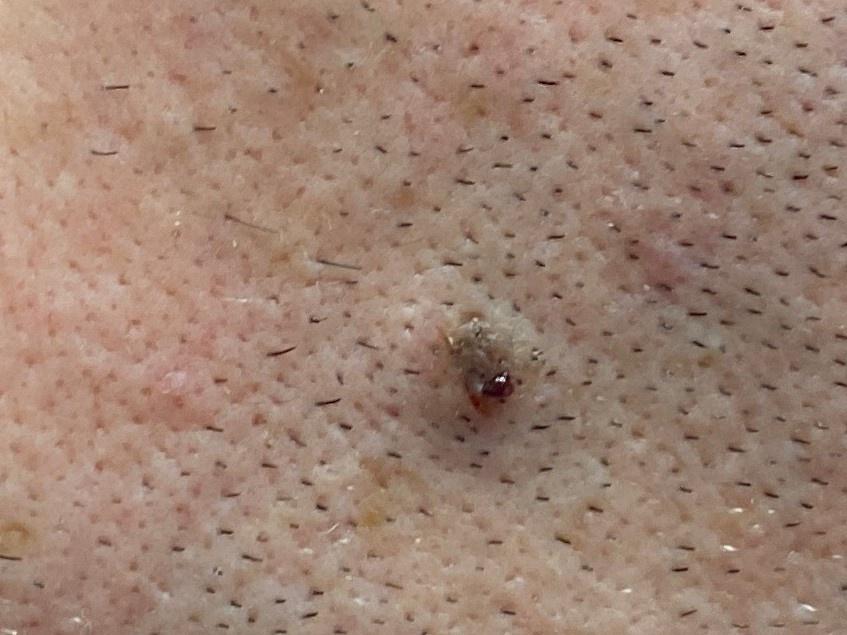image — clinical photograph; patient — male, roughly 40 years of age; melanoma history — a prior melanoma; body site — the head or neck; diagnosis — Nevus (clinical impression).